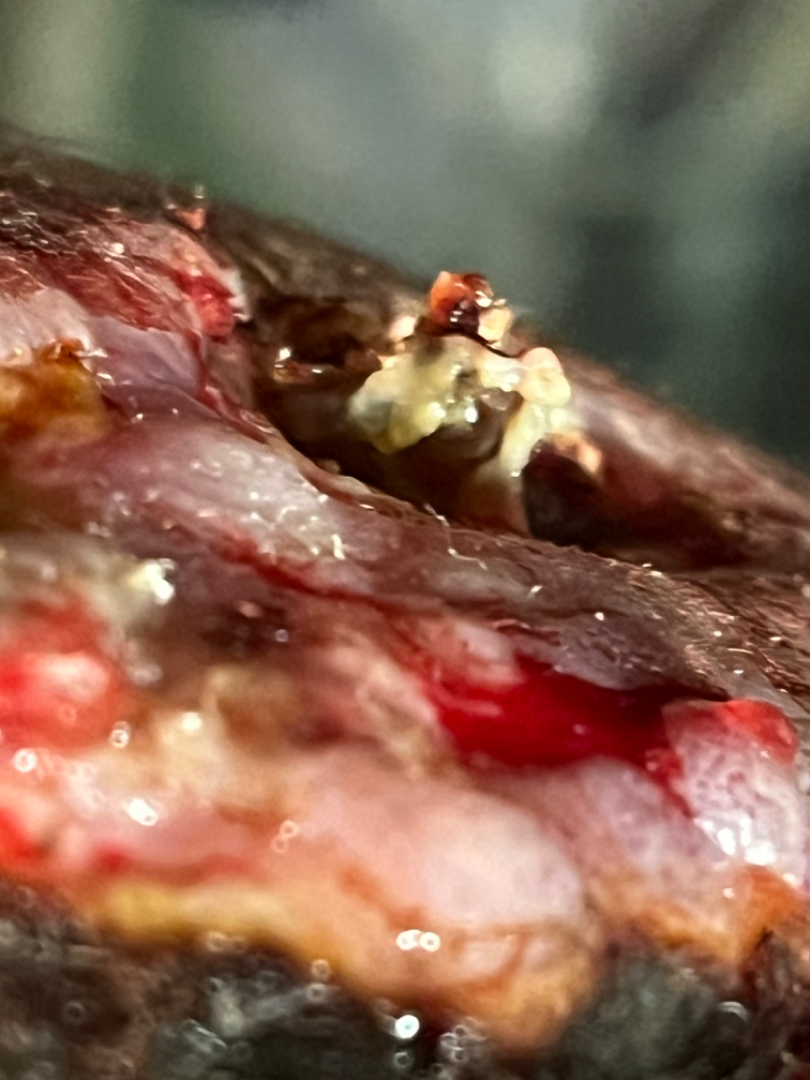{
  "assessment": "ungradable on photographic review",
  "texture": [
    "rough or flaky",
    "raised or bumpy",
    "fluid-filled"
  ],
  "systemic_symptoms": [
    "joint pain",
    "fatigue"
  ],
  "body_site": "leg",
  "shot_type": "close-up",
  "duration": "three to twelve months"
}